The subject is a male roughly 60 years of age; a dermoscopic image of a skin lesion:
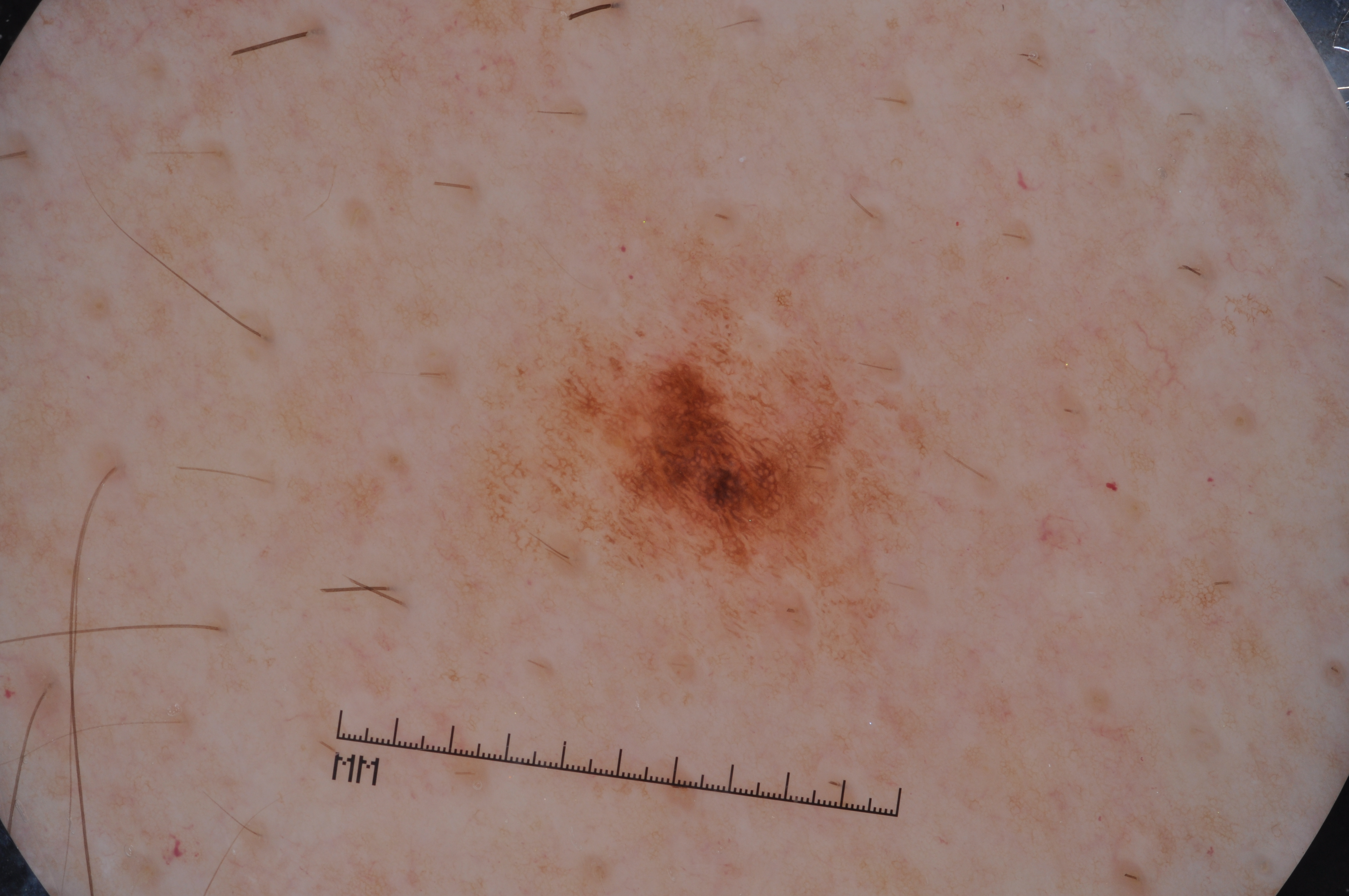Findings:
– dermoscopic findings · pigment network; absent: streaks, negative network, and milia-like cysts
– extent · ~5% of the field
– location · [548,337,896,574]
– impression · a melanocytic nevus, a benign skin lesion